The photograph is a close-up of the affected area, located on the leg: 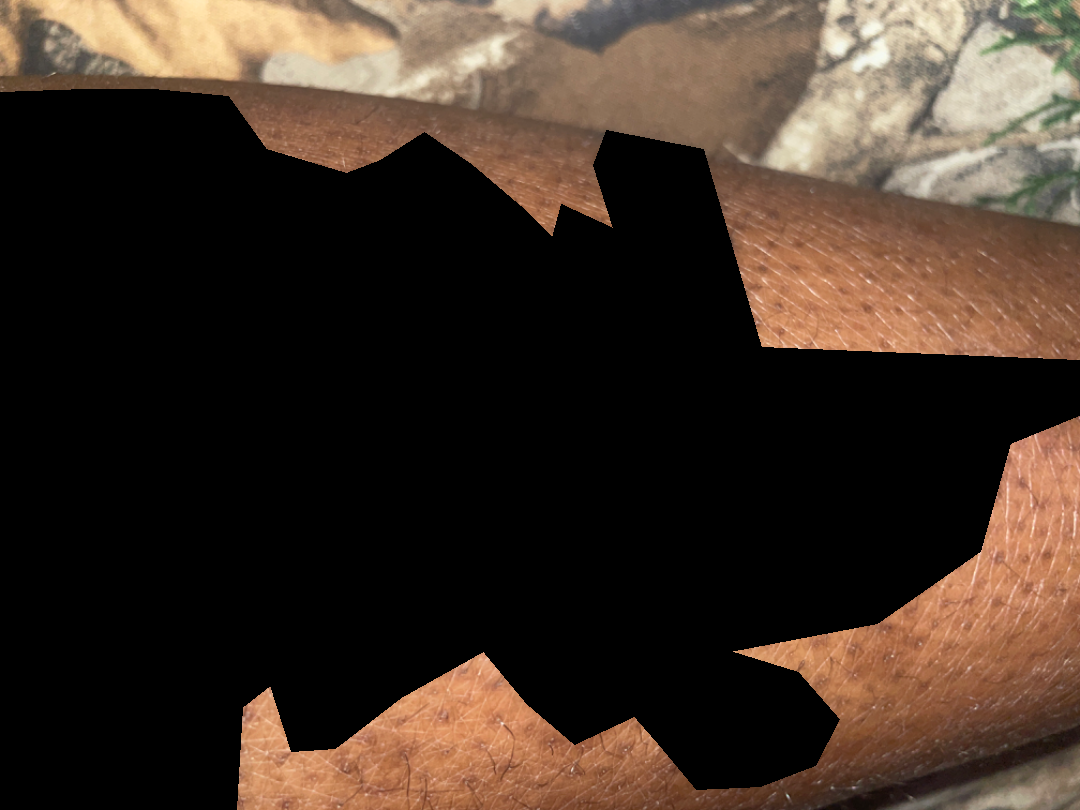assessment: indeterminate